The lesion involves the head or neck and back of the torso, an image taken at an angle, skin tone: non-clinician graders estimated Monk skin tone scale 3 or 4 (two reviewer pools), reported duration is less than one week: 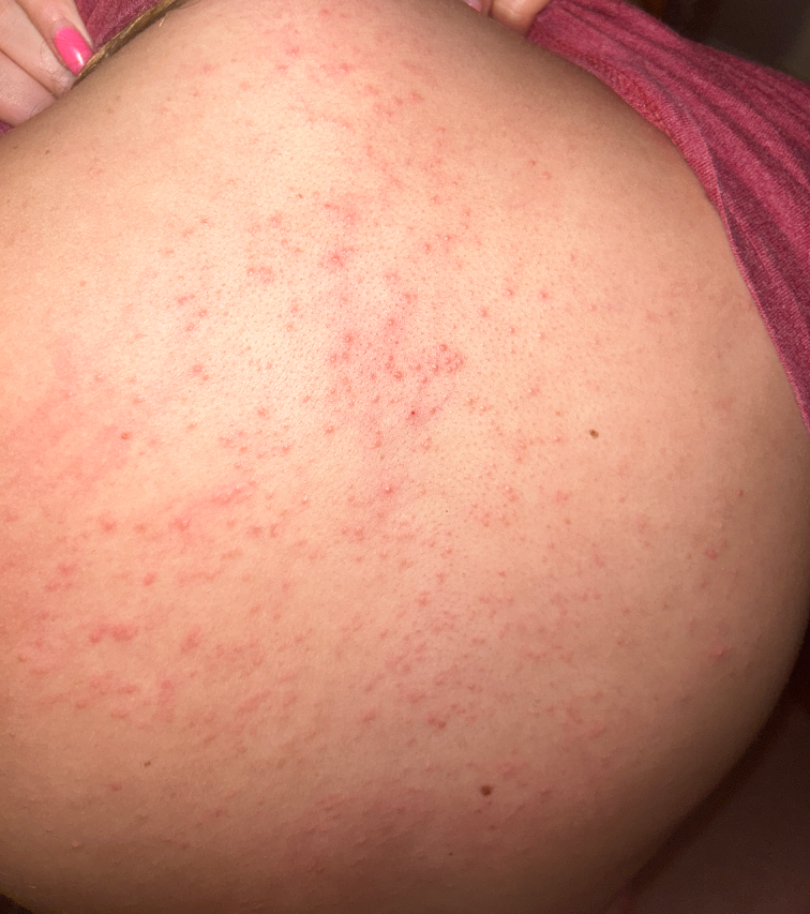Q: What is the dermatologist's impression?
A: the leading consideration is Folliculitis; an alternative is Acne